Located on the back of the torso, arm and back of the hand · the subject is male · an image taken at a distance.
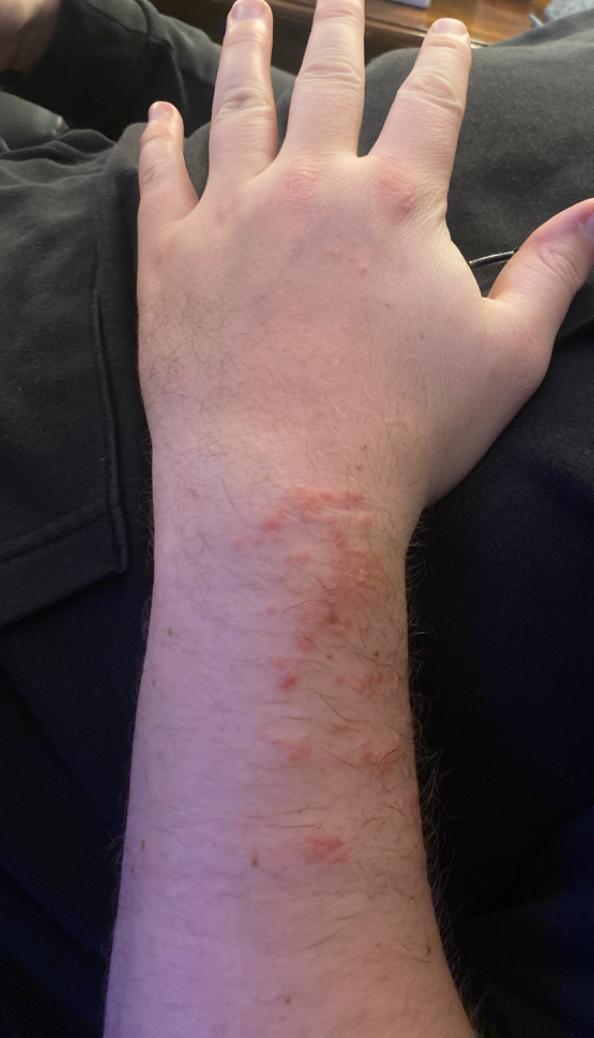Background:
The patient considered this a rash. Texture is reported as fluid-filled, raised or bumpy and rough or flaky. No constitutional symptoms were reported.
Findings:
Allergic Contact Dermatitis (leading); Impetigo (considered); Eczema (considered).